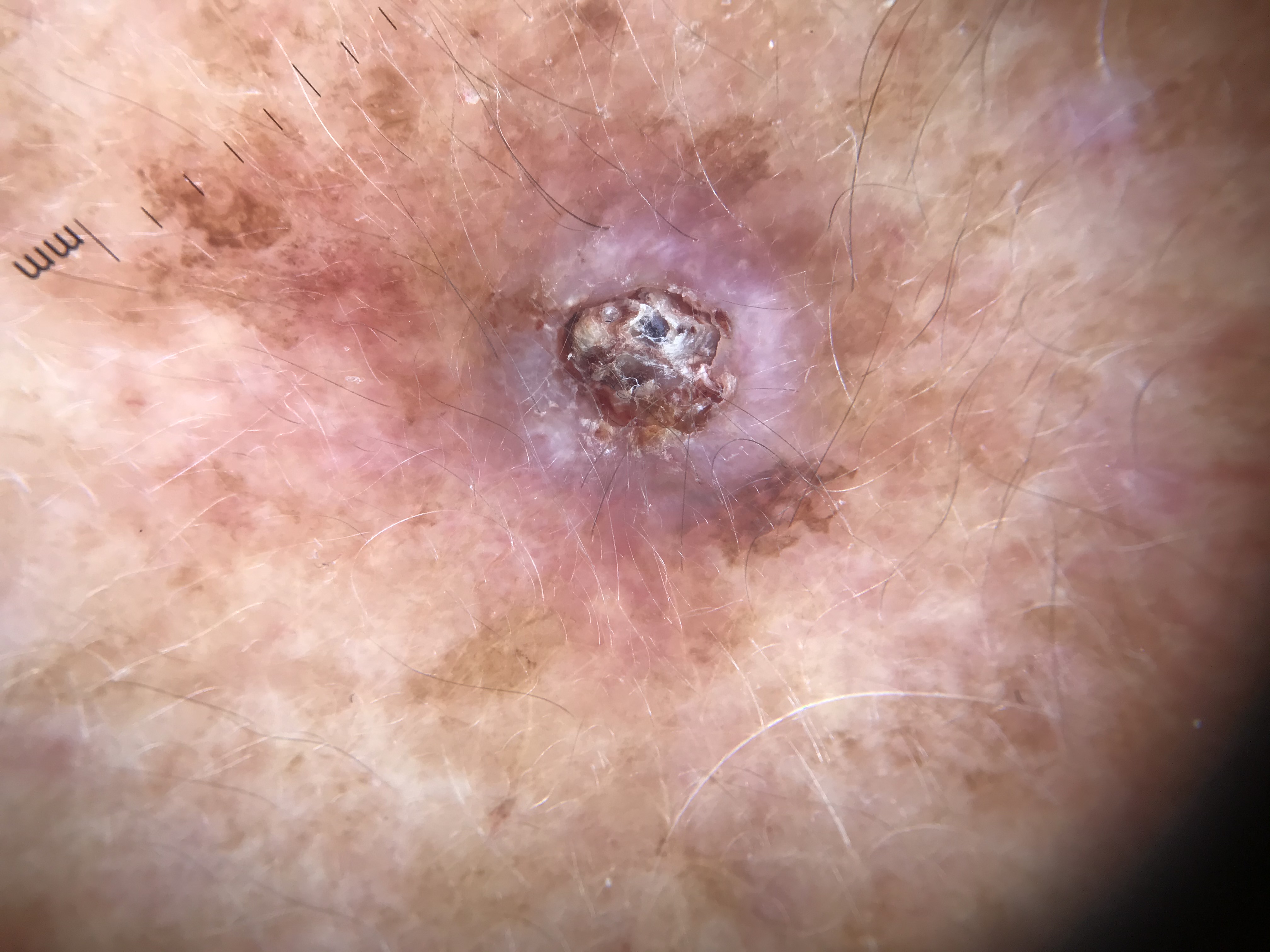| feature | finding |
|---|---|
| modality | dermoscopy |
| pathology | squamous cell carcinoma (biopsy-proven) |